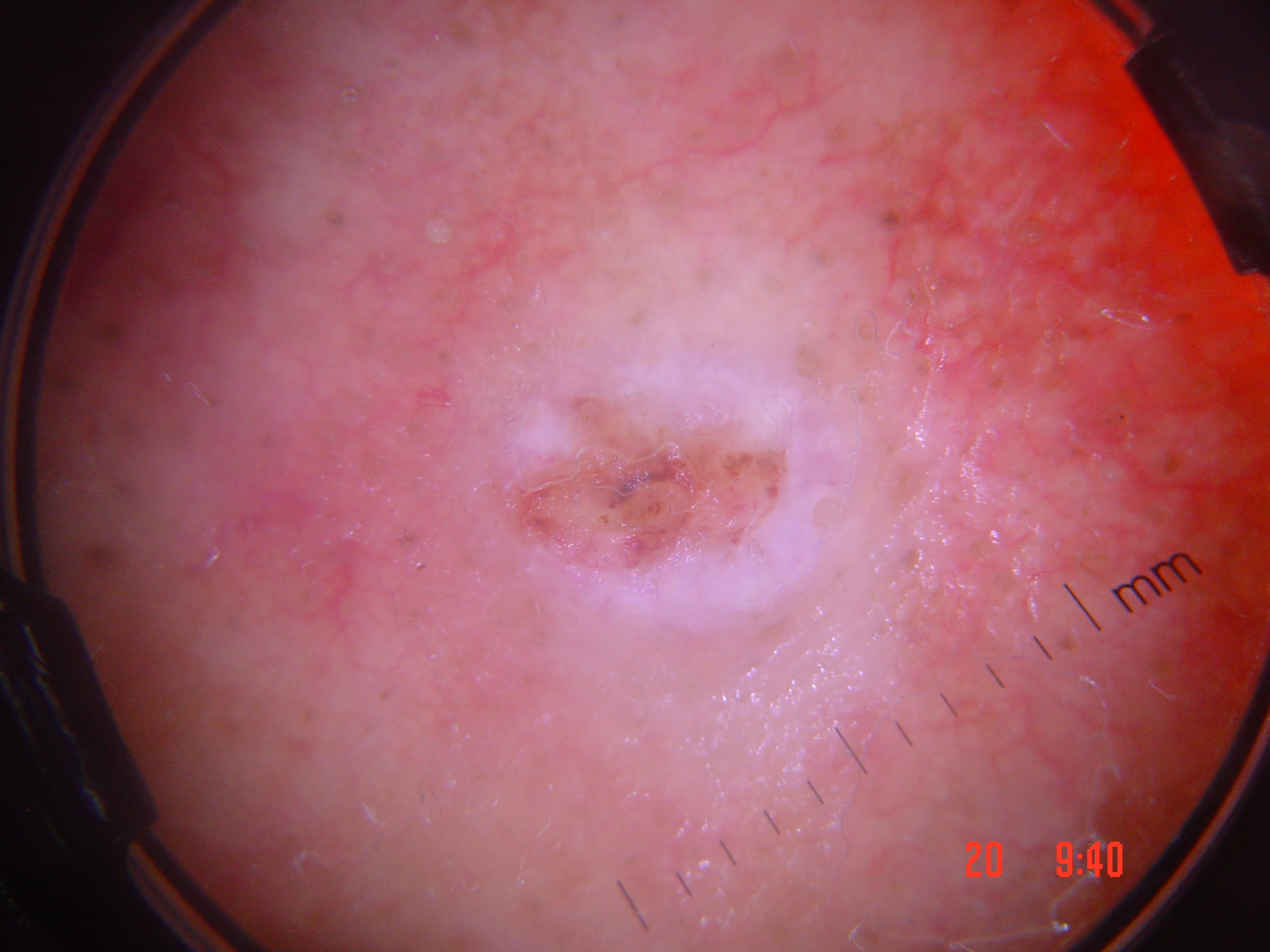Summary: A dermoscopic image of a skin lesion. The morphology is that of a keratinocytic lesion. Diagnosis: Confirmed on histopathology as a malignancy — a squamous cell carcinoma.